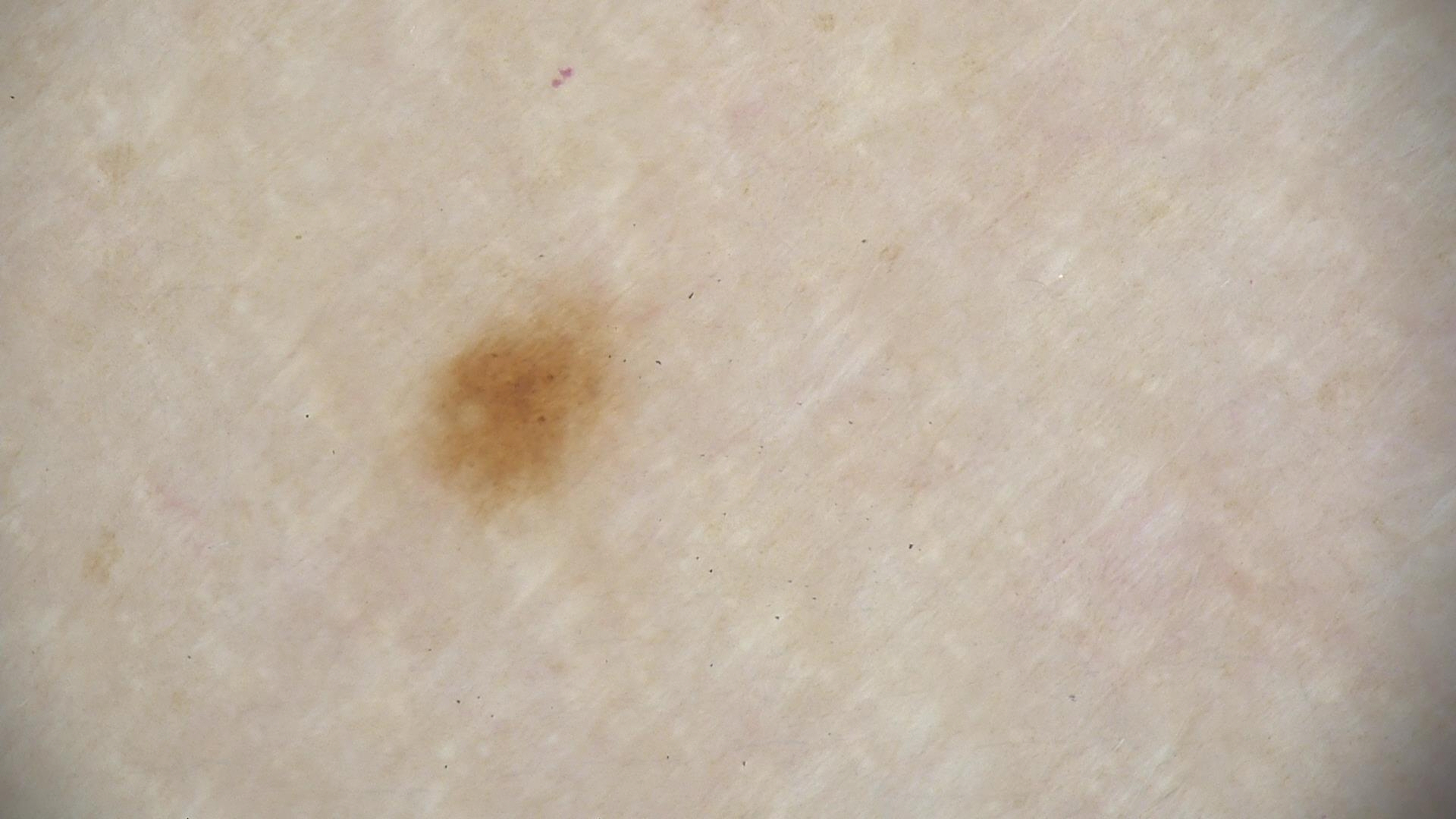Findings:
A skin lesion imaged with a dermatoscope.
Impression:
Consistent with a dysplastic junctional nevus.